Dermoscopy of a skin lesion · a female patient aged 53-57 · the patient was assessed as Fitzpatrick II — 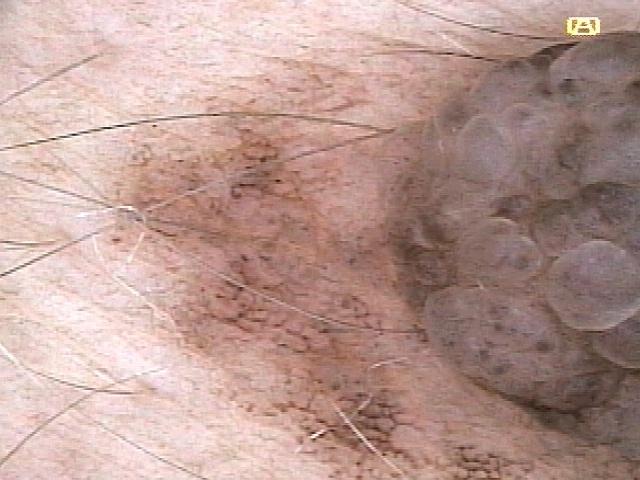Located on the trunk (the anterior trunk). The clinical impression was a benign, melanocytic lesion — a nevus.